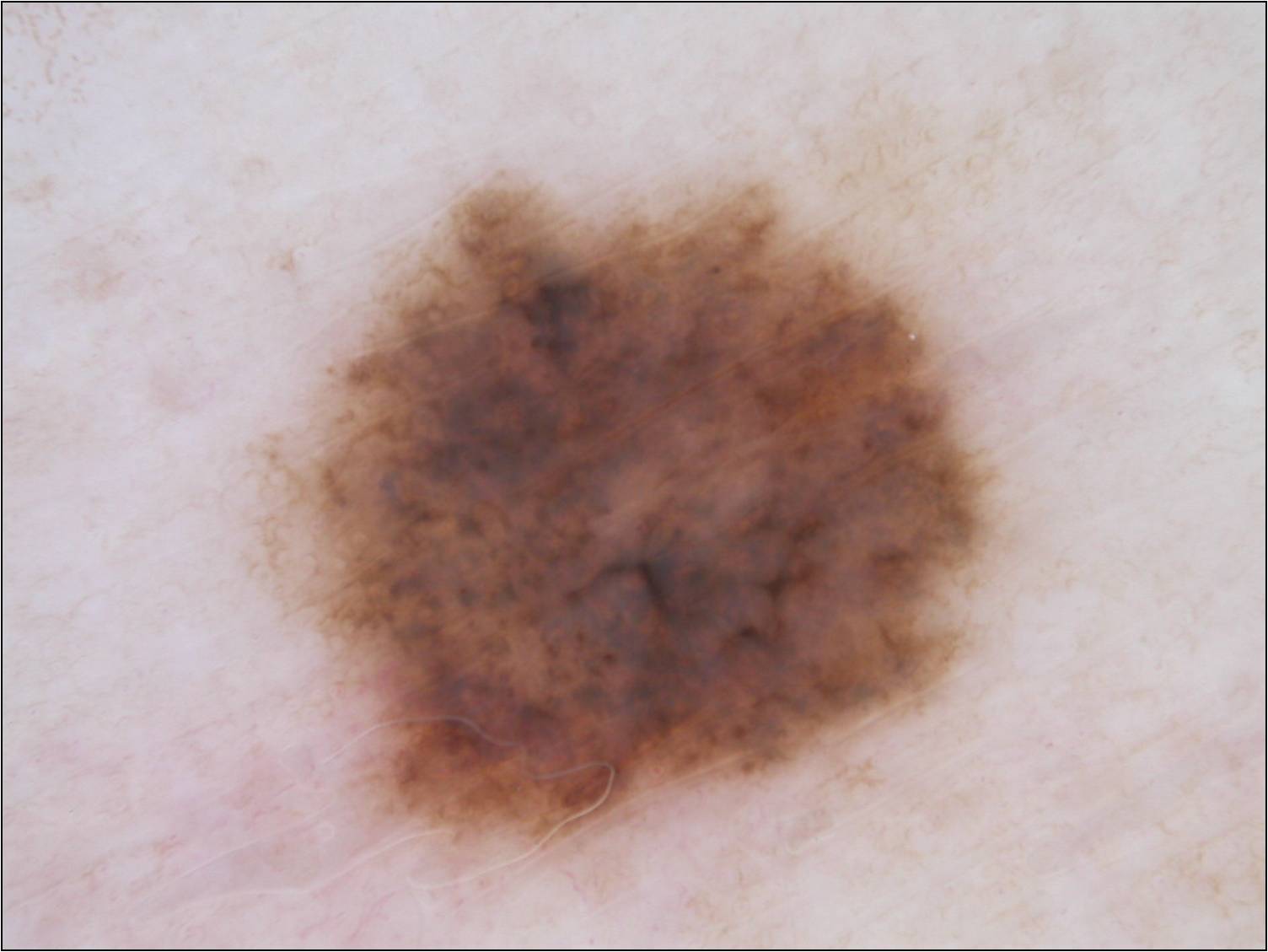A dermoscopic image of a skin lesion.
A female subject about 35 years old.
In (x1, y1, x2, y2) order, the visible lesion spans 261 172 1012 872.
The dermoscopic pattern shows globules and pigment network; no milia-like cysts, streaks, or negative network.
Diagnosed as a melanocytic nevus.